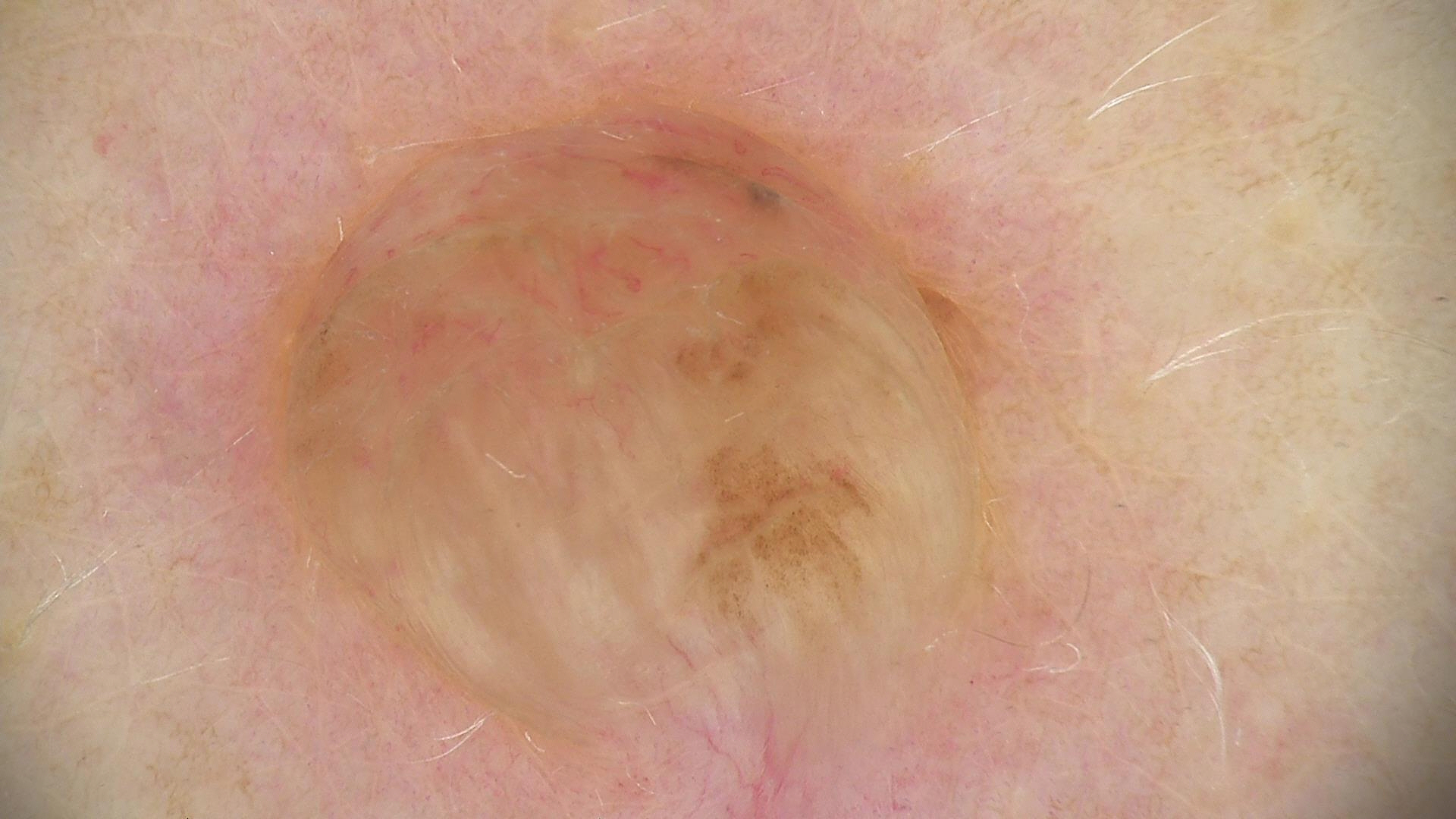category — banal
label — dermal nevus (expert consensus)